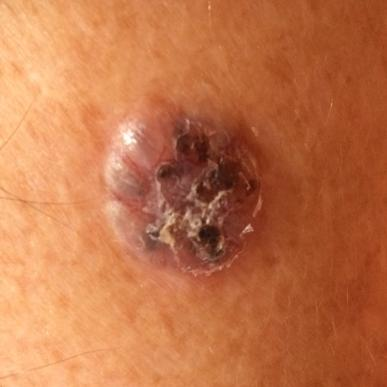A clinical photograph of a skin lesion. A male patient in their early 70s. The patient was assessed as Fitzpatrick skin type II. By history, prior malignancy (patient or family) and pesticide exposure. The lesion is on an arm. The lesion is roughly 15 by 13 mm. By the patient's account, the lesion is elevated, has grown, hurts, itches, and has bled, but has not changed. Histopathologically confirmed as a basal cell carcinoma.